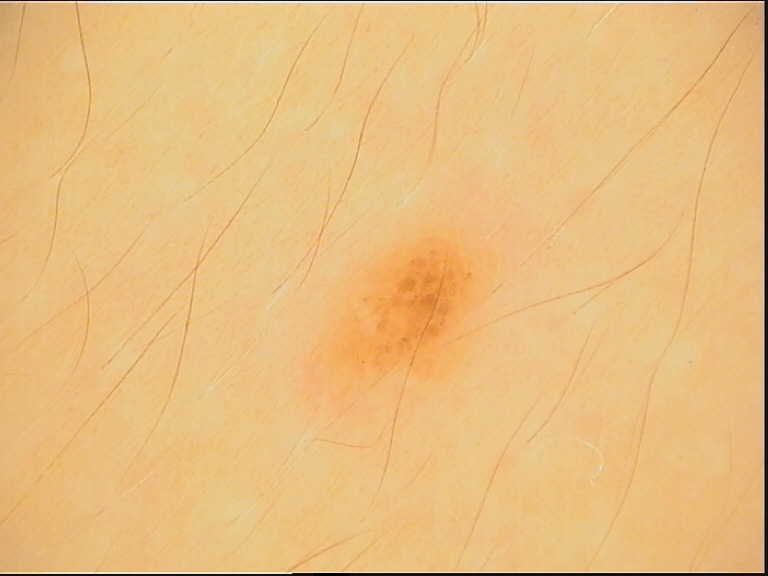A dermoscopic image of a skin lesion. This is a banal lesion. The diagnosis was a junctional nevus.